A dermoscopic image of a skin lesion:
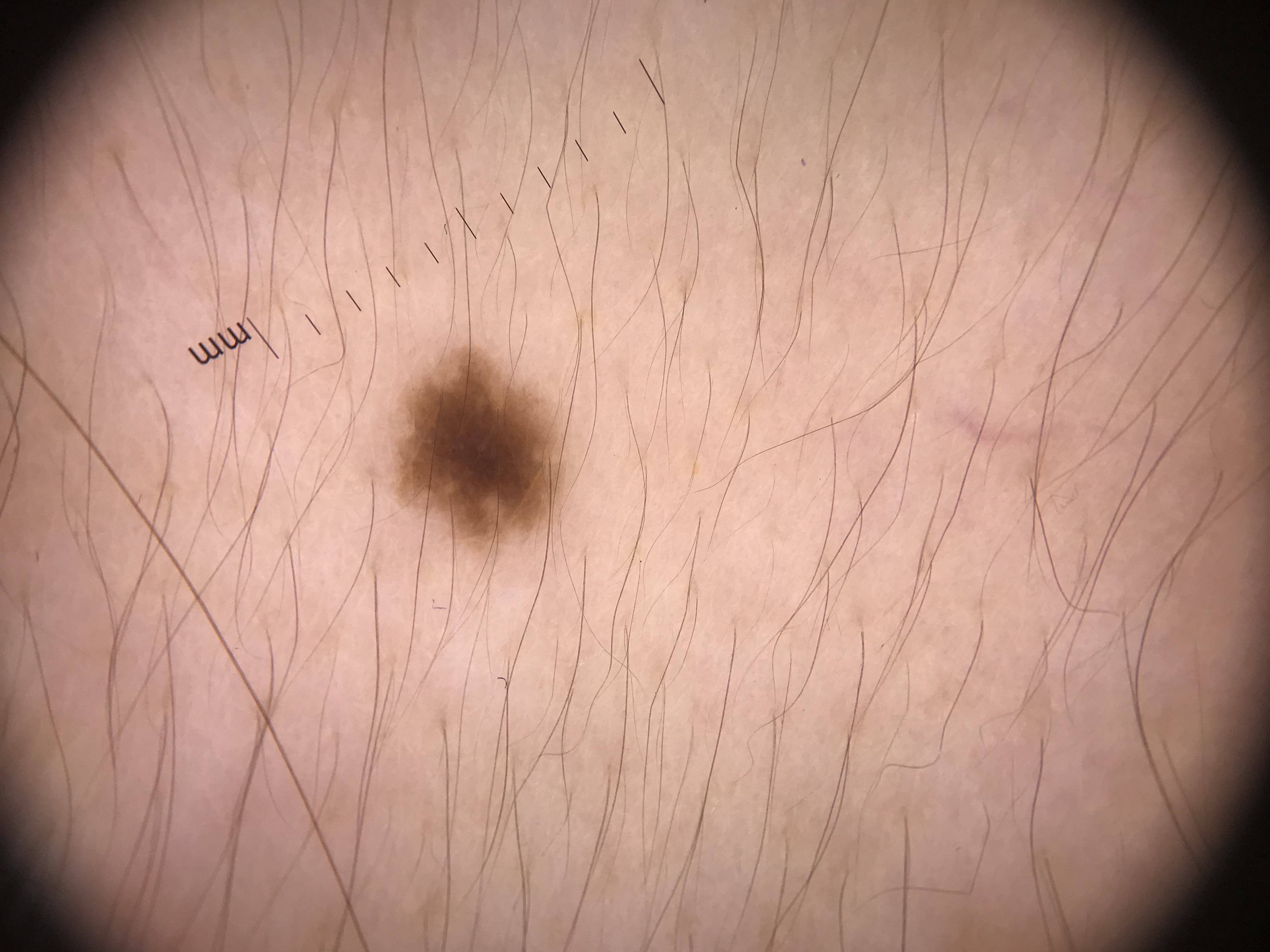Q: What is the lesion category?
A: banal
Q: What was the diagnostic impression?
A: junctional nevus (expert consensus)